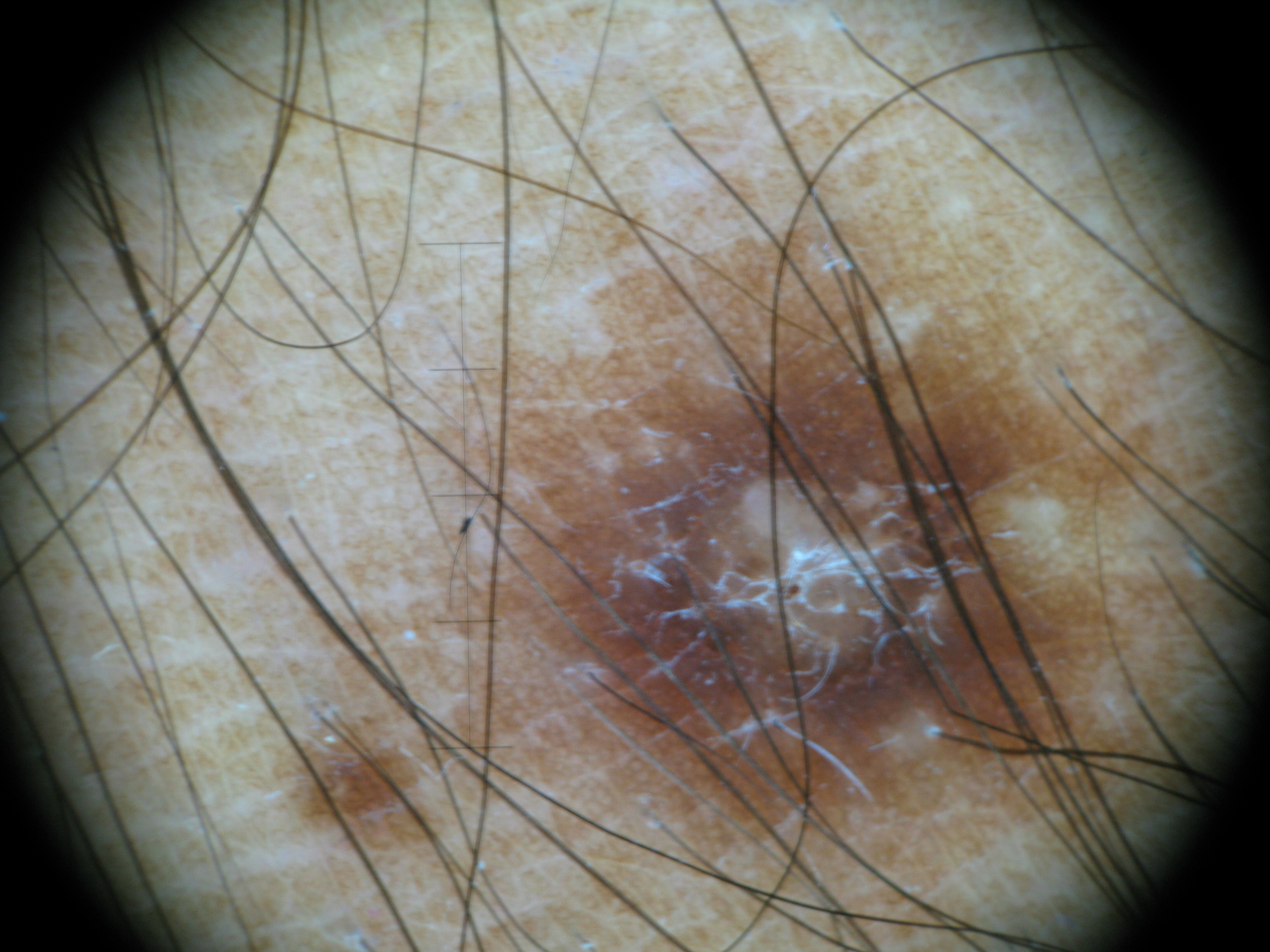The diagnosis was a dermatofibroma.